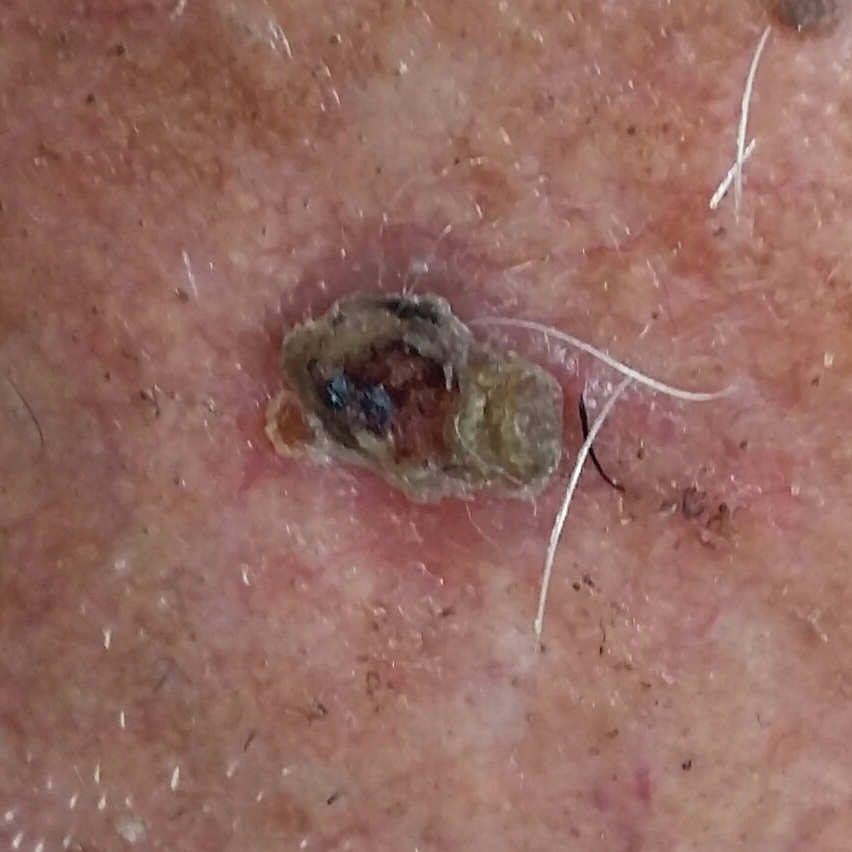Case summary: The patient was assessed as FST II. A clinical close-up photograph of a skin lesion. The chart notes alcohol use, pesticide exposure, prior skin cancer (patient or family), and prior malignancy (patient or family). Located on the face. Measuring about 15 × 13 mm. The patient reports that the lesion has bled, itches, hurts, and is elevated, but has not grown. Diagnosis: Histopathologically confirmed as a basal cell carcinoma.